Located on the front of the torso and leg · close-up view · the subject is 18–29, female:
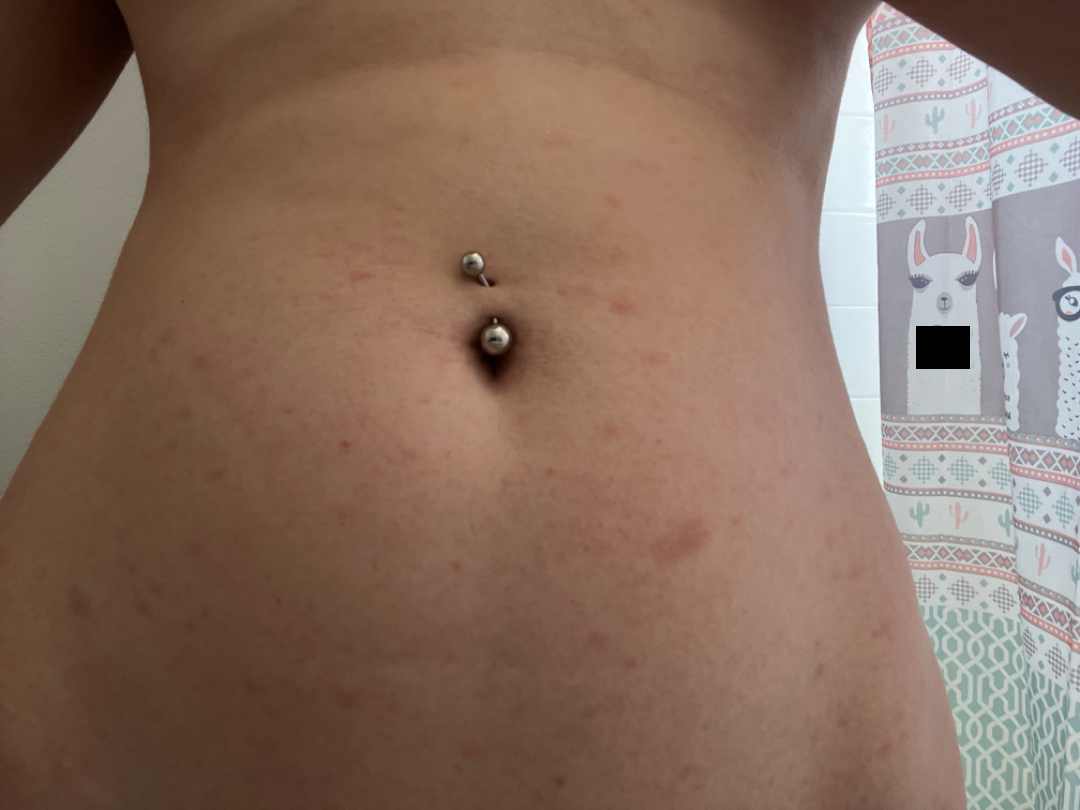On dermatologist assessment of the image, the leading impression is Pityriasis rosea; also on the differential is Psoriasis; also raised was Eczema.